A dermoscopic image of a skin lesion:
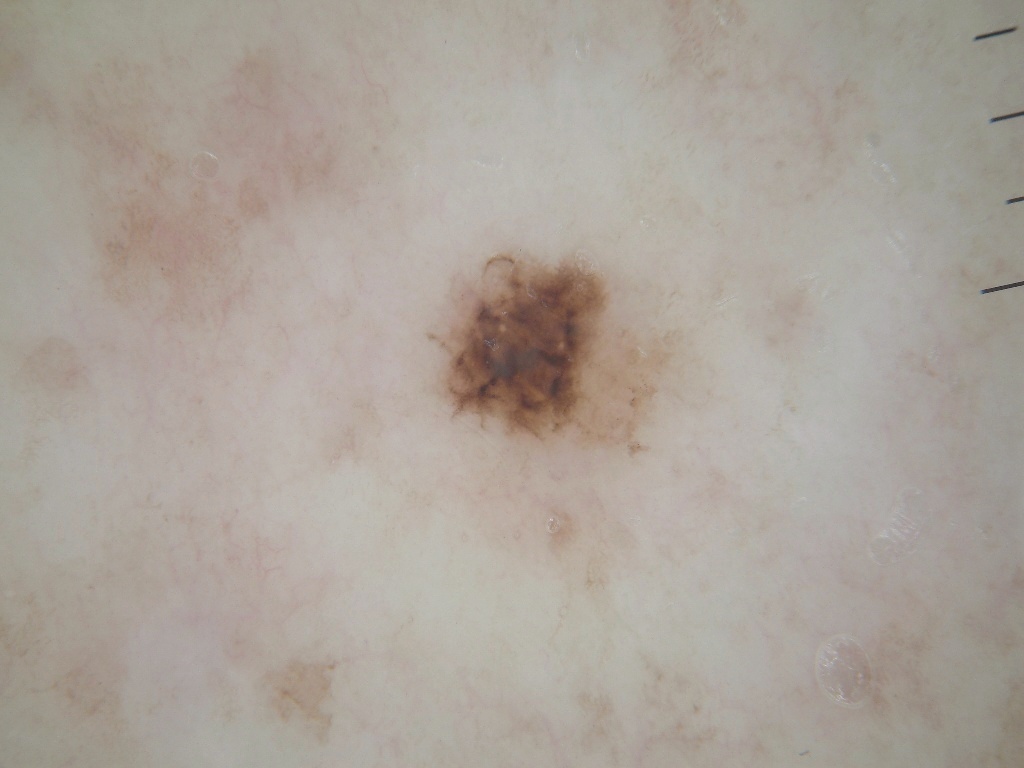Q: Where is the lesion located?
A: bbox=[422, 238, 693, 460]
Q: What is this lesion?
A: a benign skin lesion